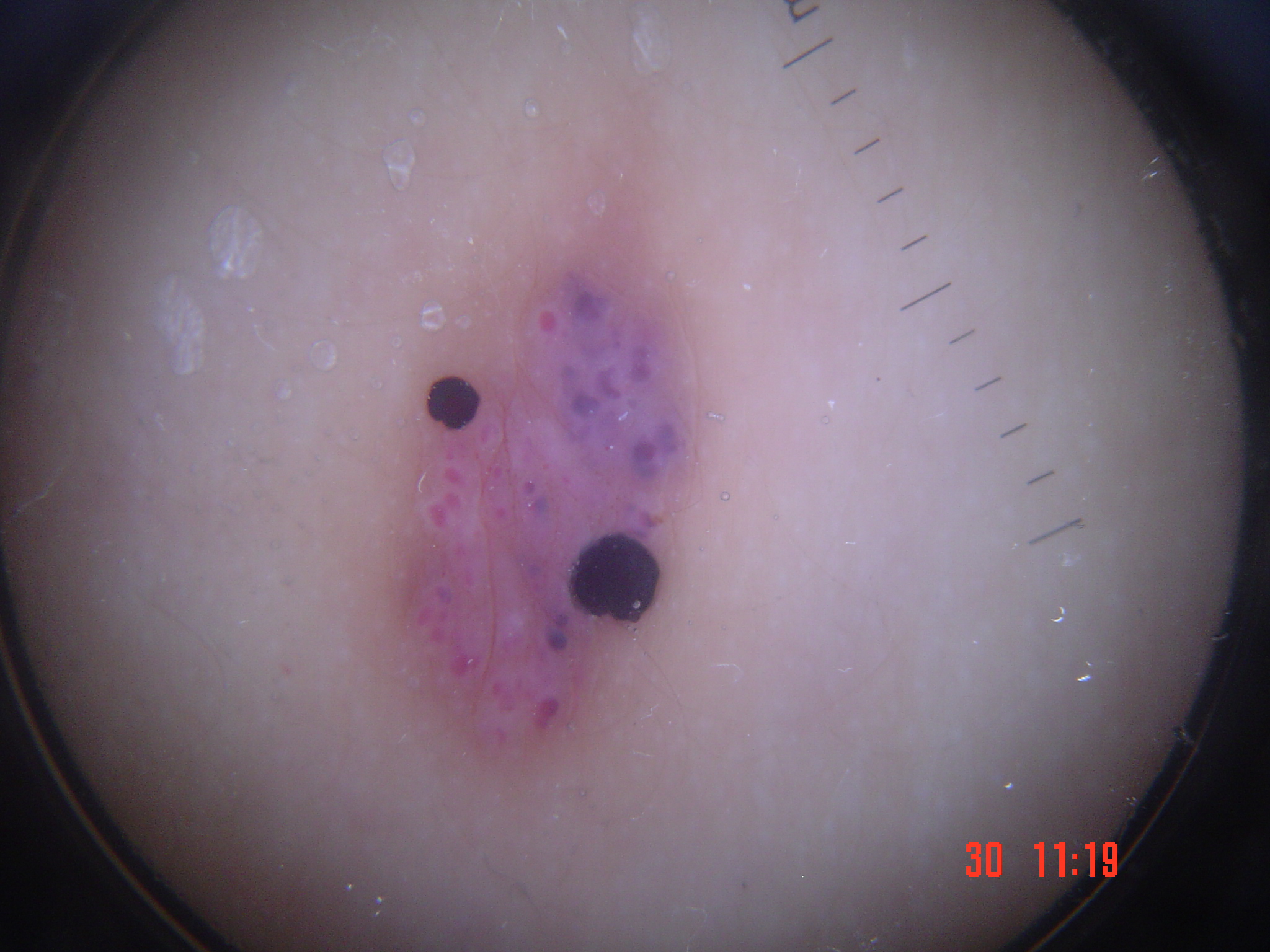image type=dermoscopy | category=vascular | diagnosis=angiokeratoma (expert consensus).